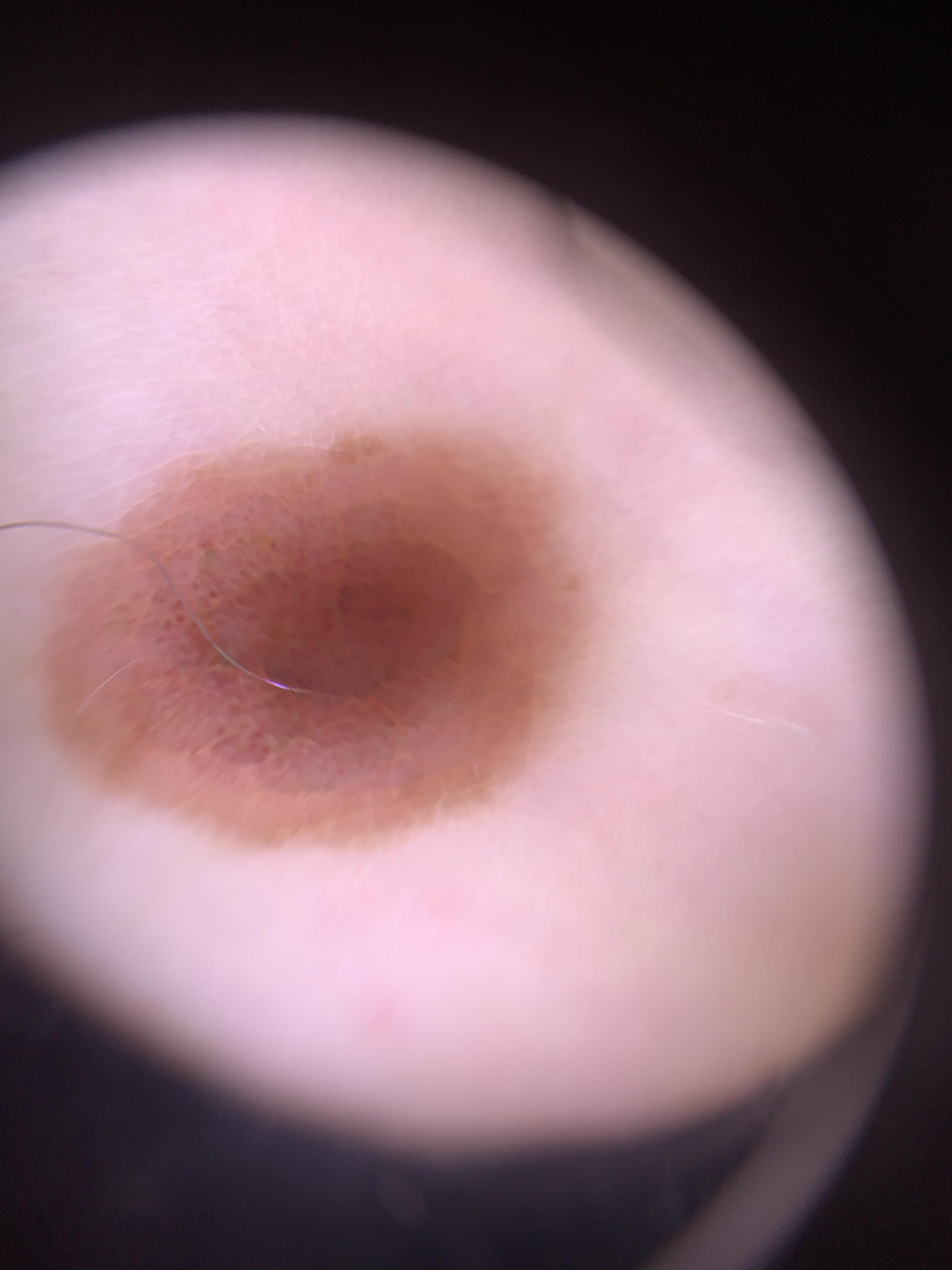Notes:
- patient: female, in their mid-40s
- anatomic site: the trunk (the anterior trunk)
- impression: Nevus